A skin lesion imaged with a dermatoscope:
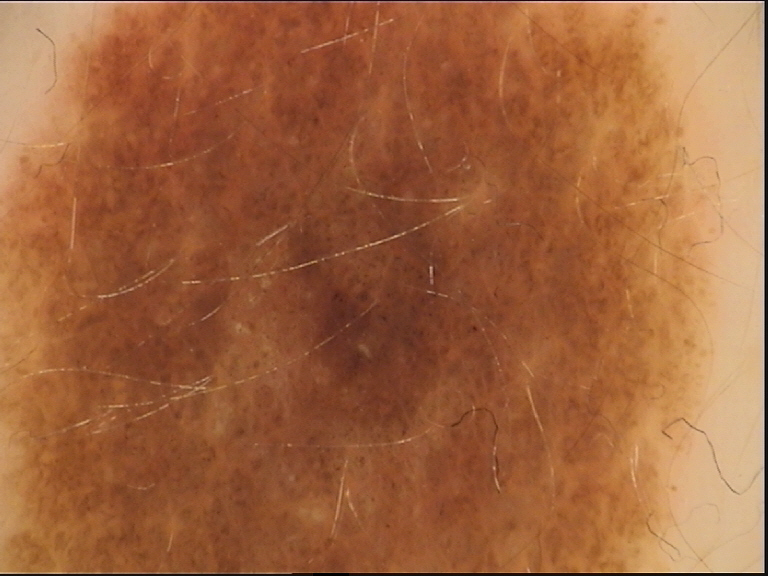| feature | finding |
|---|---|
| label | dysplastic compound nevus (expert consensus) |